A dermoscopic image of a skin lesion: 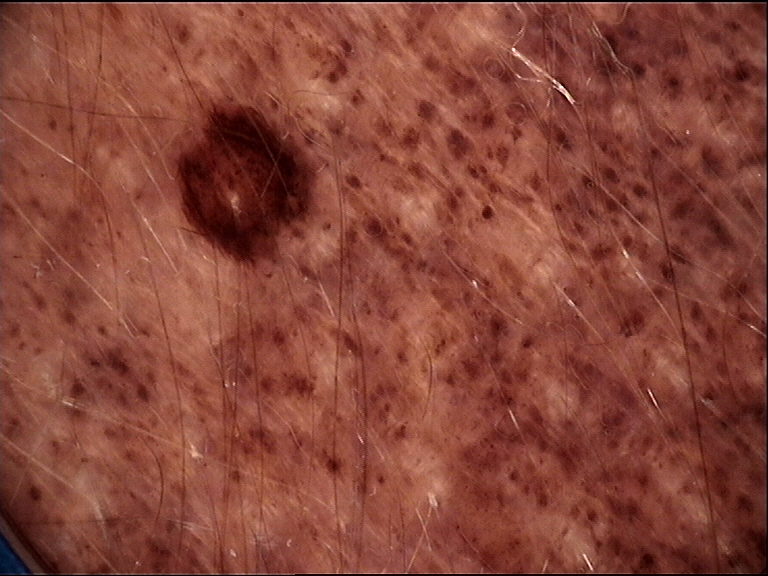diagnosis:
  name: congenital compound nevus
  code: ccb
  malignancy: benign
  super_class: melanocytic
  confirmation: expert consensus